A dermoscopic image of a skin lesion: 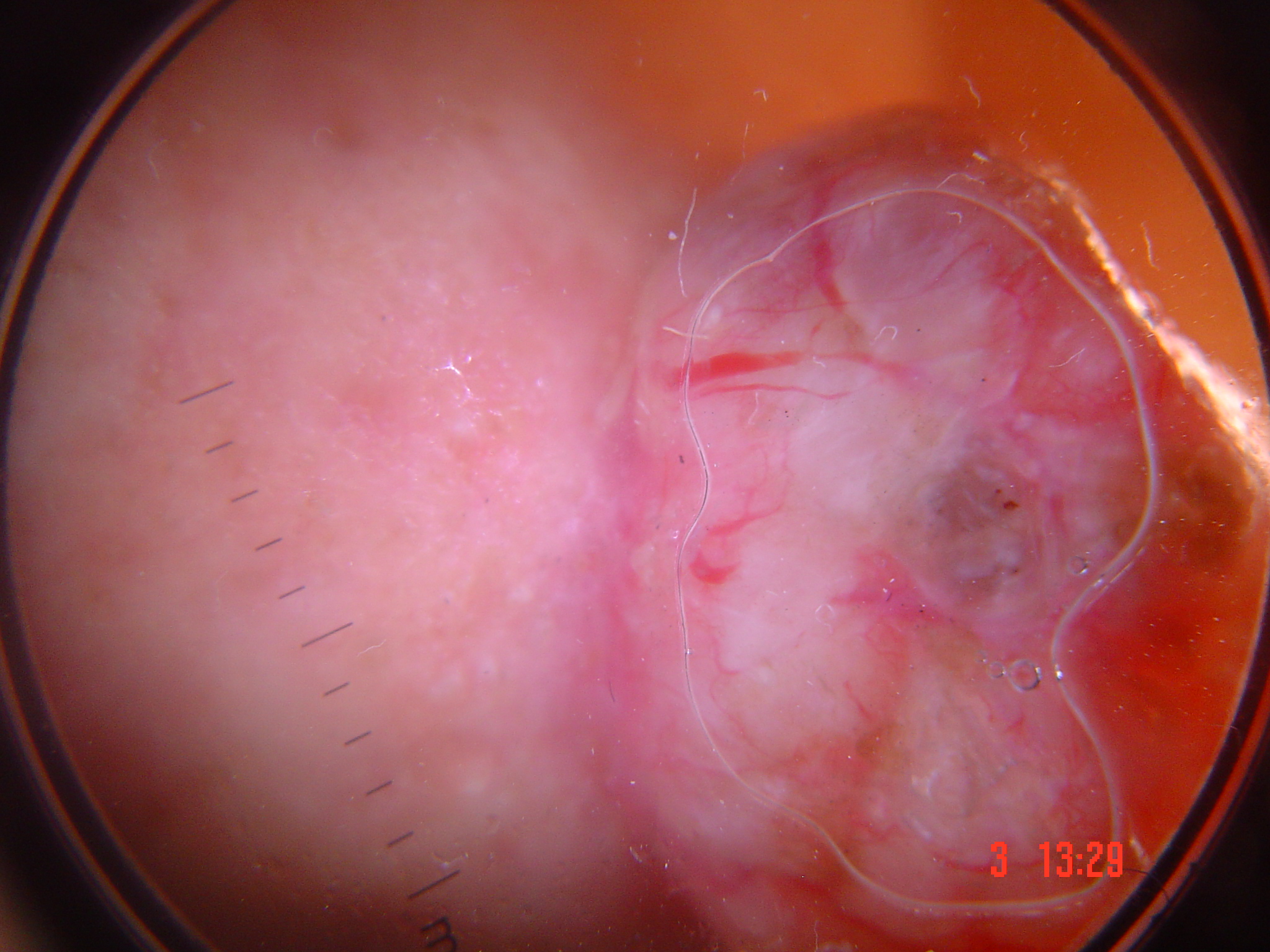Confirmed on histopathology as a basal cell carcinoma.